An overview clinical photograph of a skin lesion. A female subject in their mid-50s.
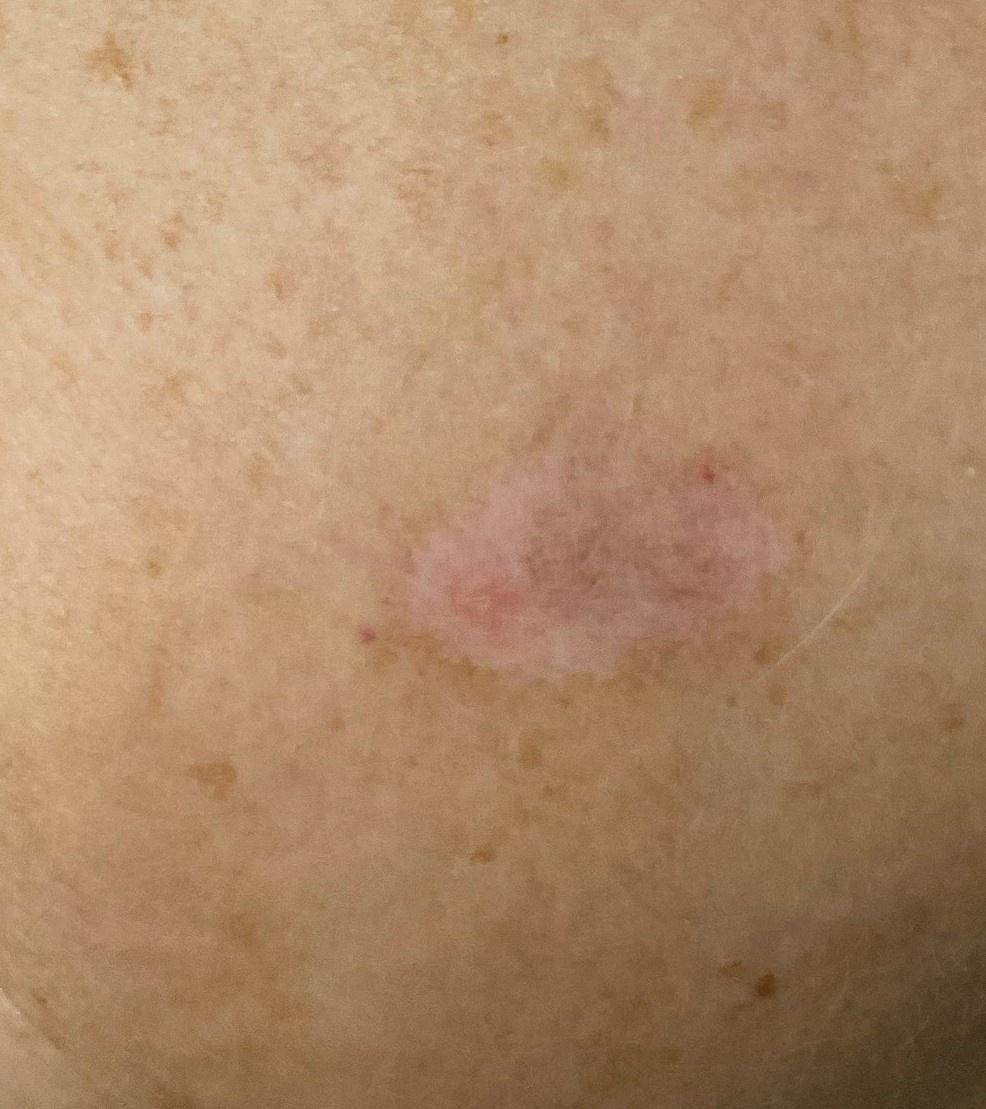{"lesion_location": {"region": "the head or neck"}, "diagnosis": {"name": "Solar or actinic keratosis", "malignancy": "indeterminate", "confirmation": "histopathology", "lineage": "epidermal"}}